A dermoscopic image of a skin lesion: 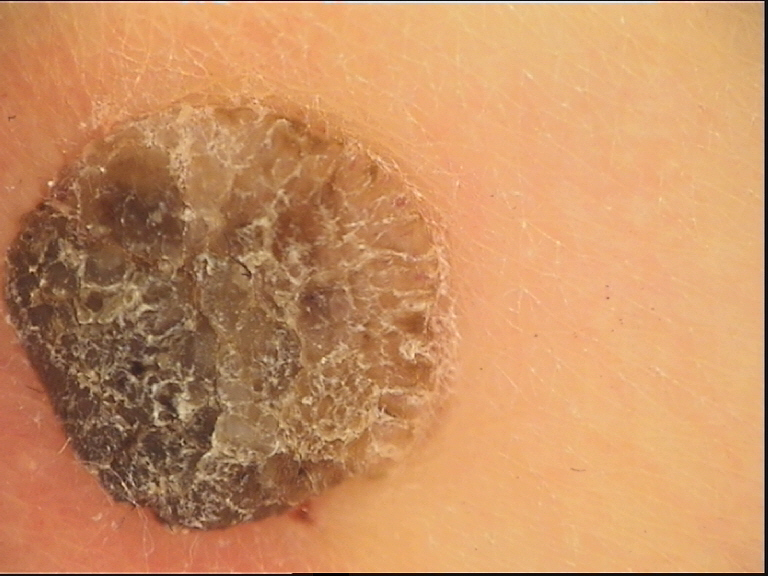This is a keratinocytic lesion. The diagnostic label was a benign lesion — a seborrheic keratosis.